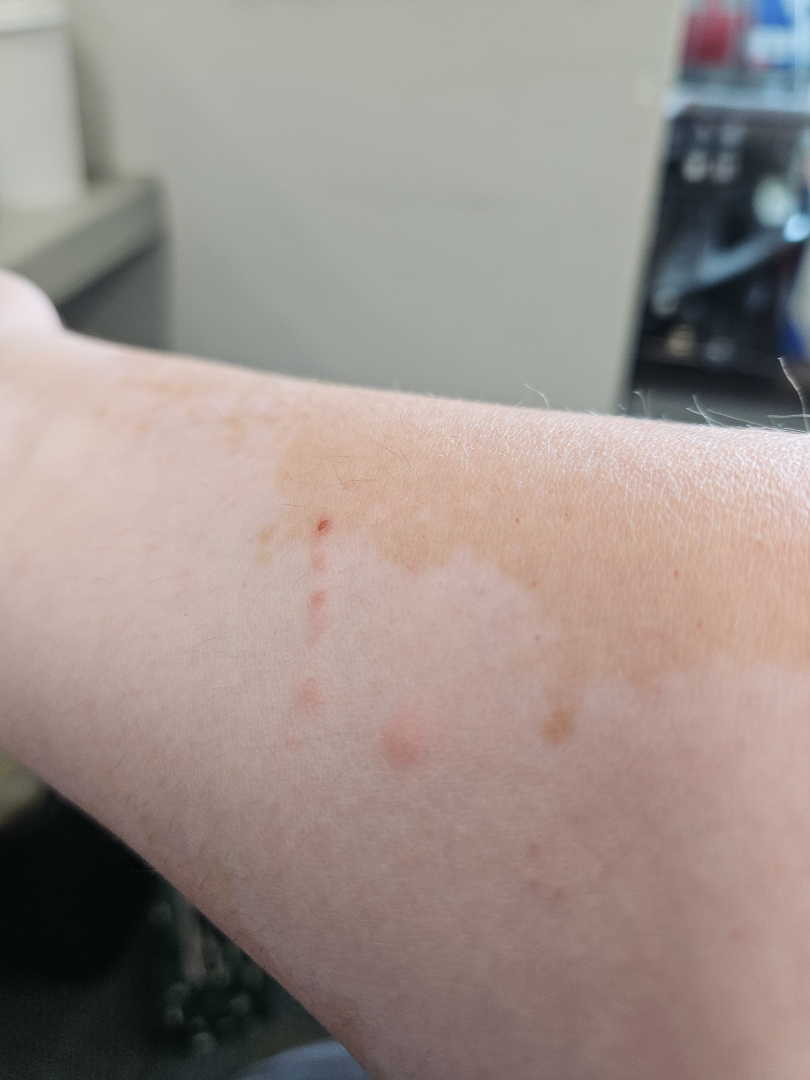Q: Anatomic location?
A: arm
Q: When did this start?
A: less than one week
Q: Patient's own categorization?
A: a rash
Q: Texture?
A: raised or bumpy
Q: Image view?
A: at an angle
Q: Who is the patient?
A: female, age 40–49